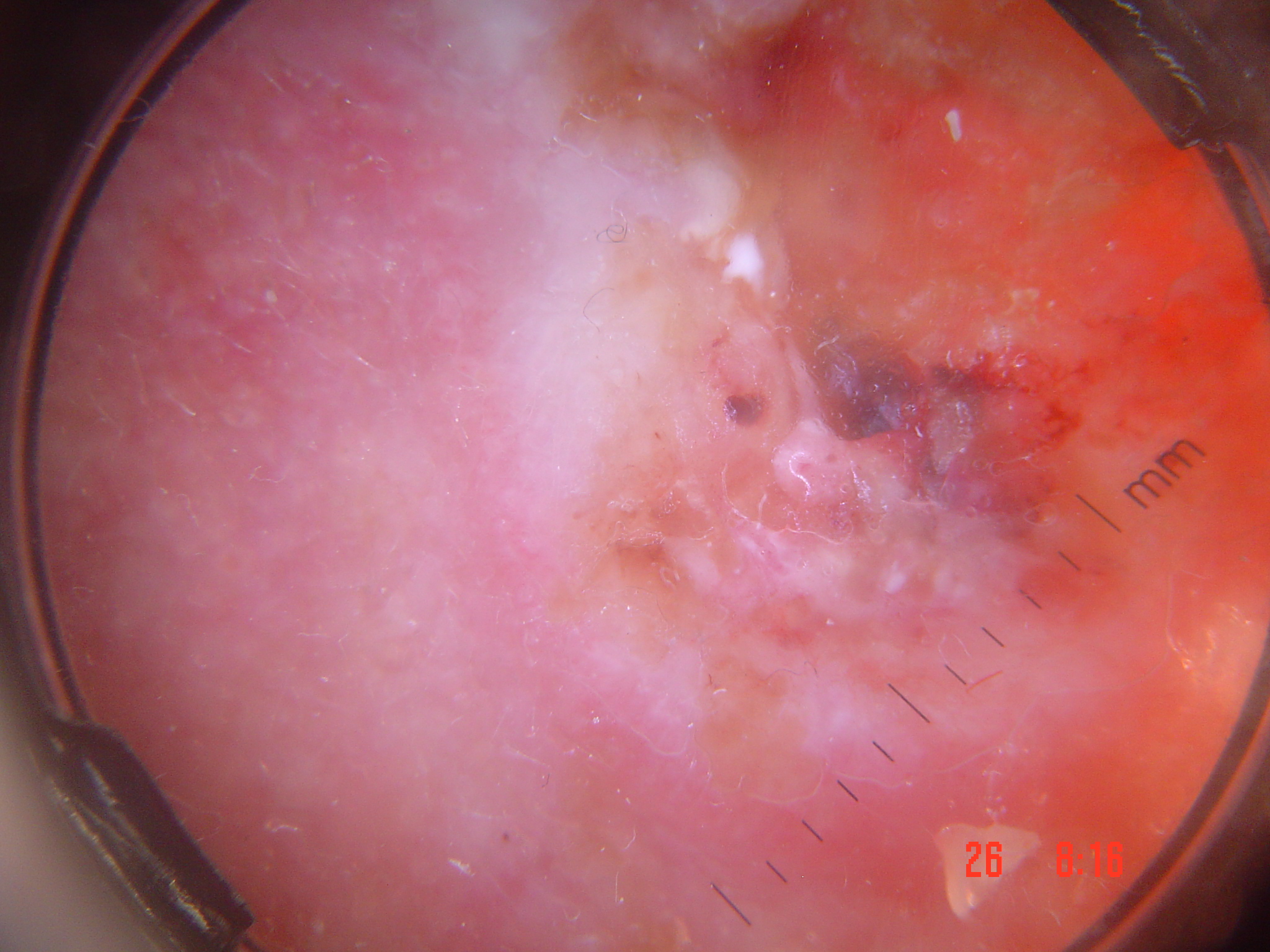{"image": "dermatoscopy", "lesion_type": {"main_class": "keratinocytic"}, "diagnosis": {"name": "squamous cell carcinoma", "code": "scc", "malignancy": "malignant", "super_class": "non-melanocytic", "confirmation": "histopathology"}}